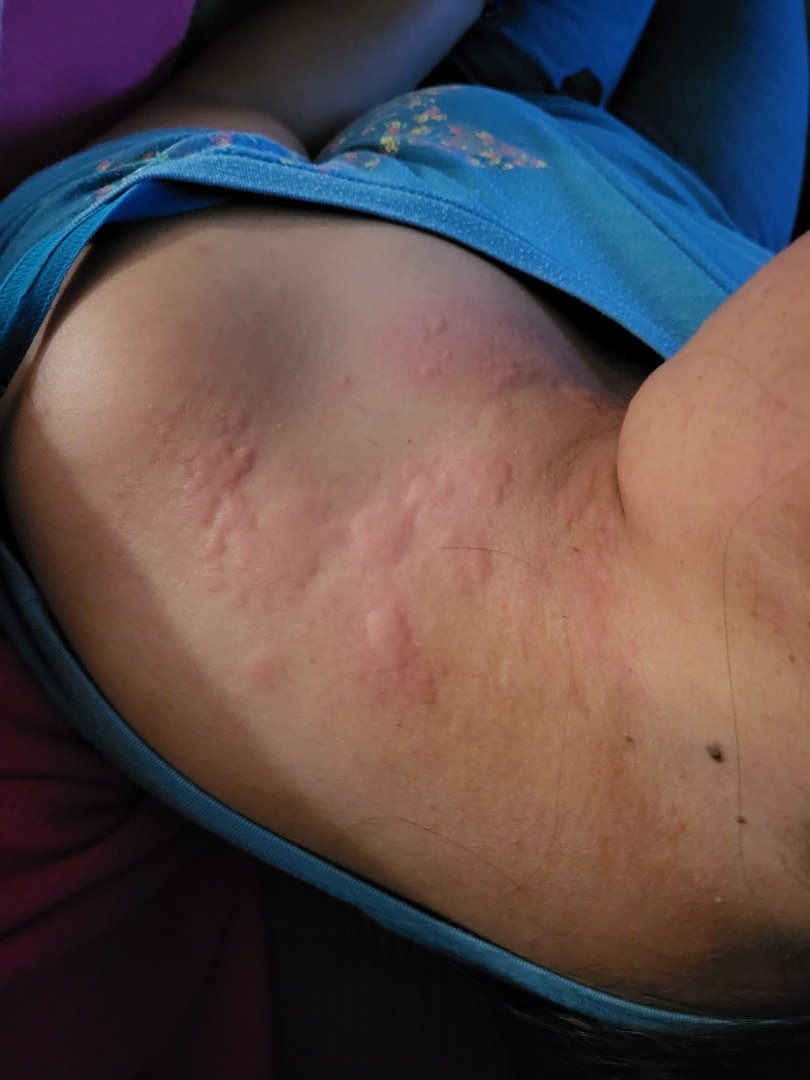diagnostic considerations = in keeping with Urticaria